The condition has been present for about one day · the photograph was taken at an angle · the patient considered this a rash · the lesion is associated with bothersome appearance and itching · skin tone: Fitzpatrick skin type III · the lesion involves the back of the torso and front of the torso · female patient, age 40–49.
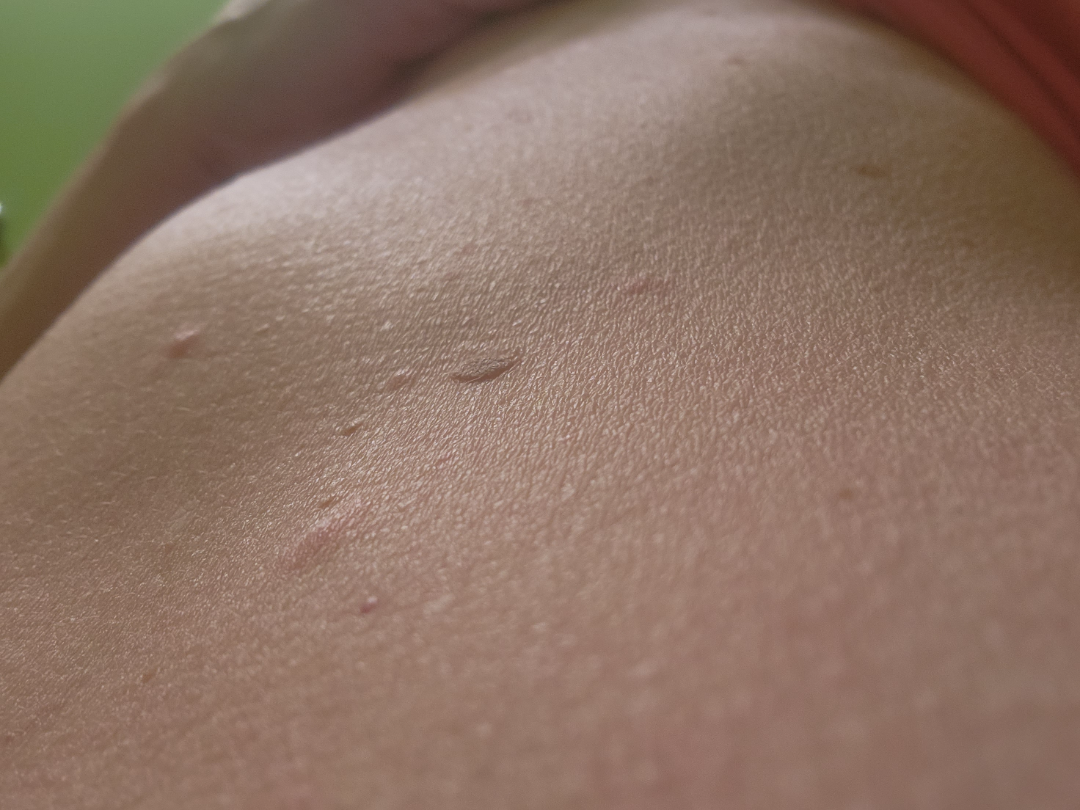  differential: Pityriasis rosea